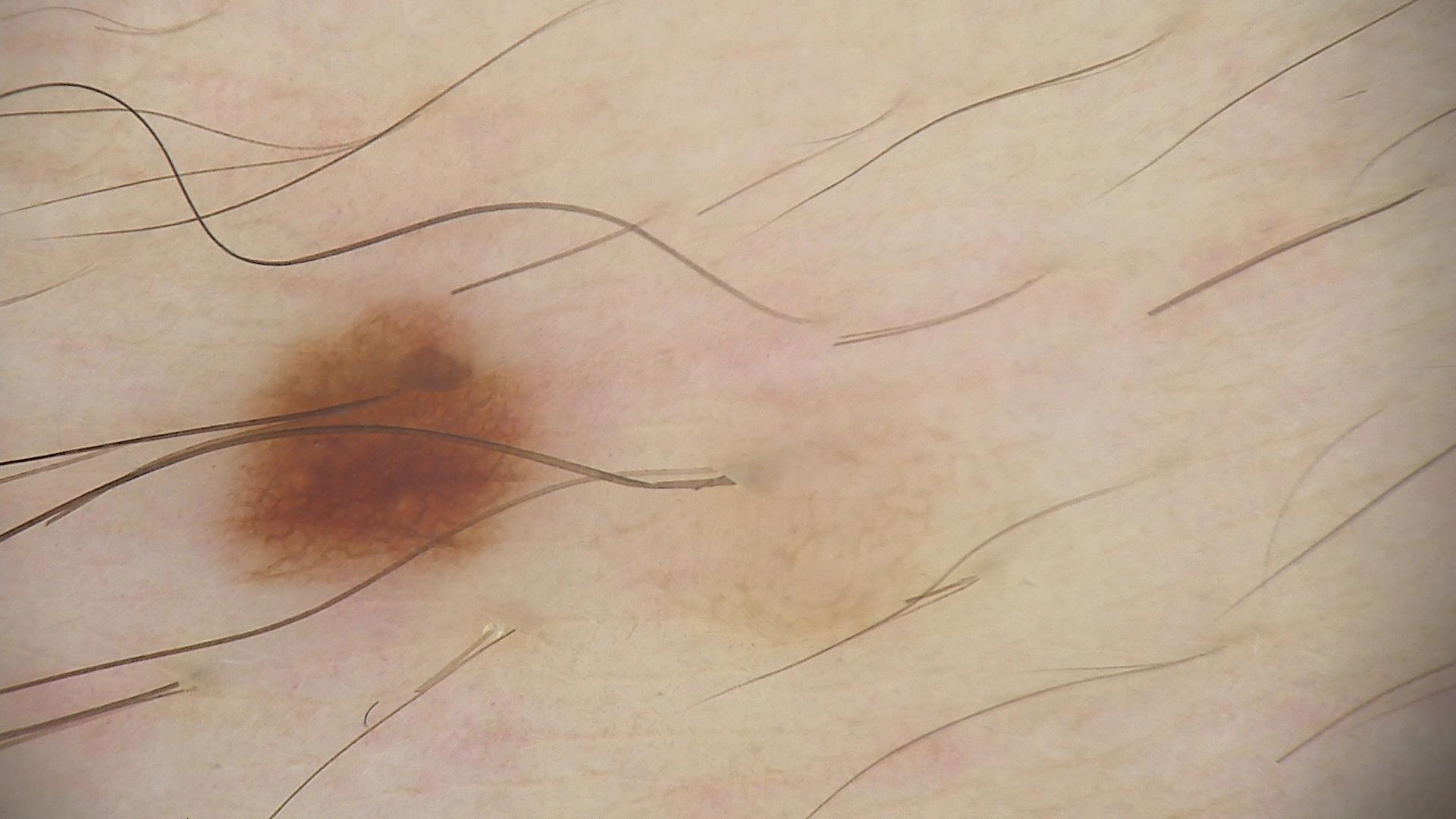A skin lesion imaged with a dermatoscope. Consistent with a benign lesion — a dysplastic junctional nevus.